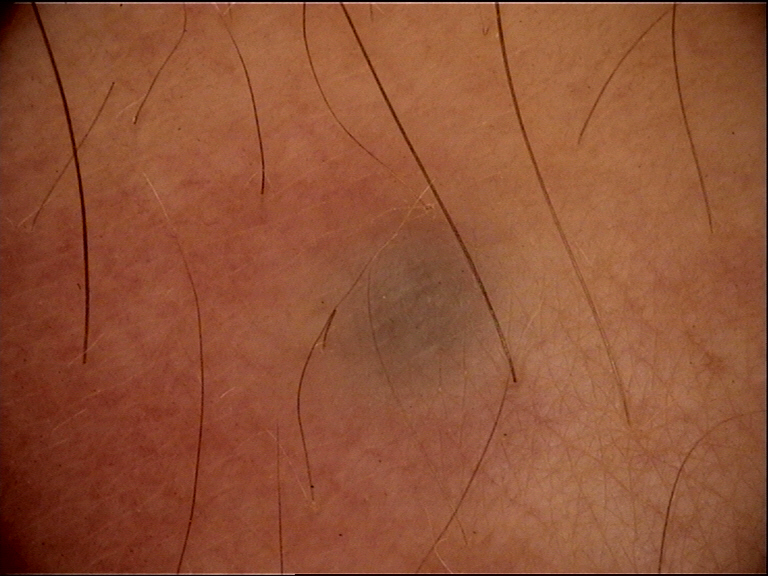Q: What is this lesion?
A: blue nevus (expert consensus)